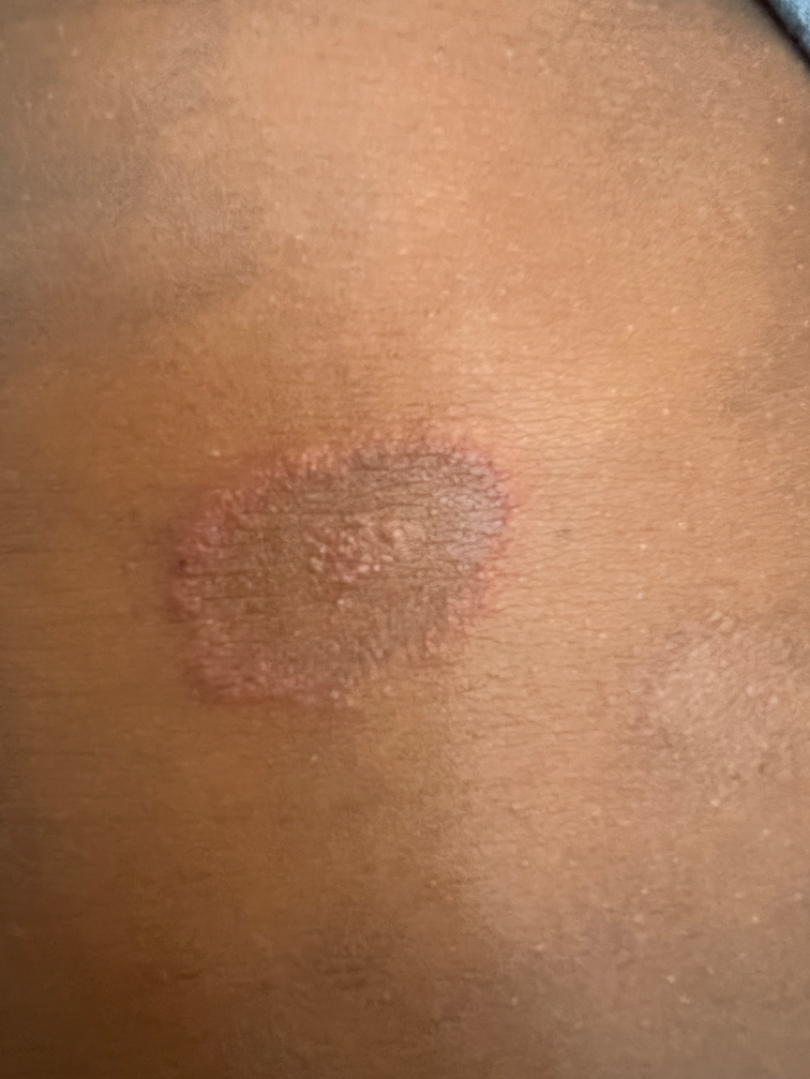Q: What is the dermatologist's impression?
A: favoring Tinea; also consider Drug Rash; less likely is Porokeratosis